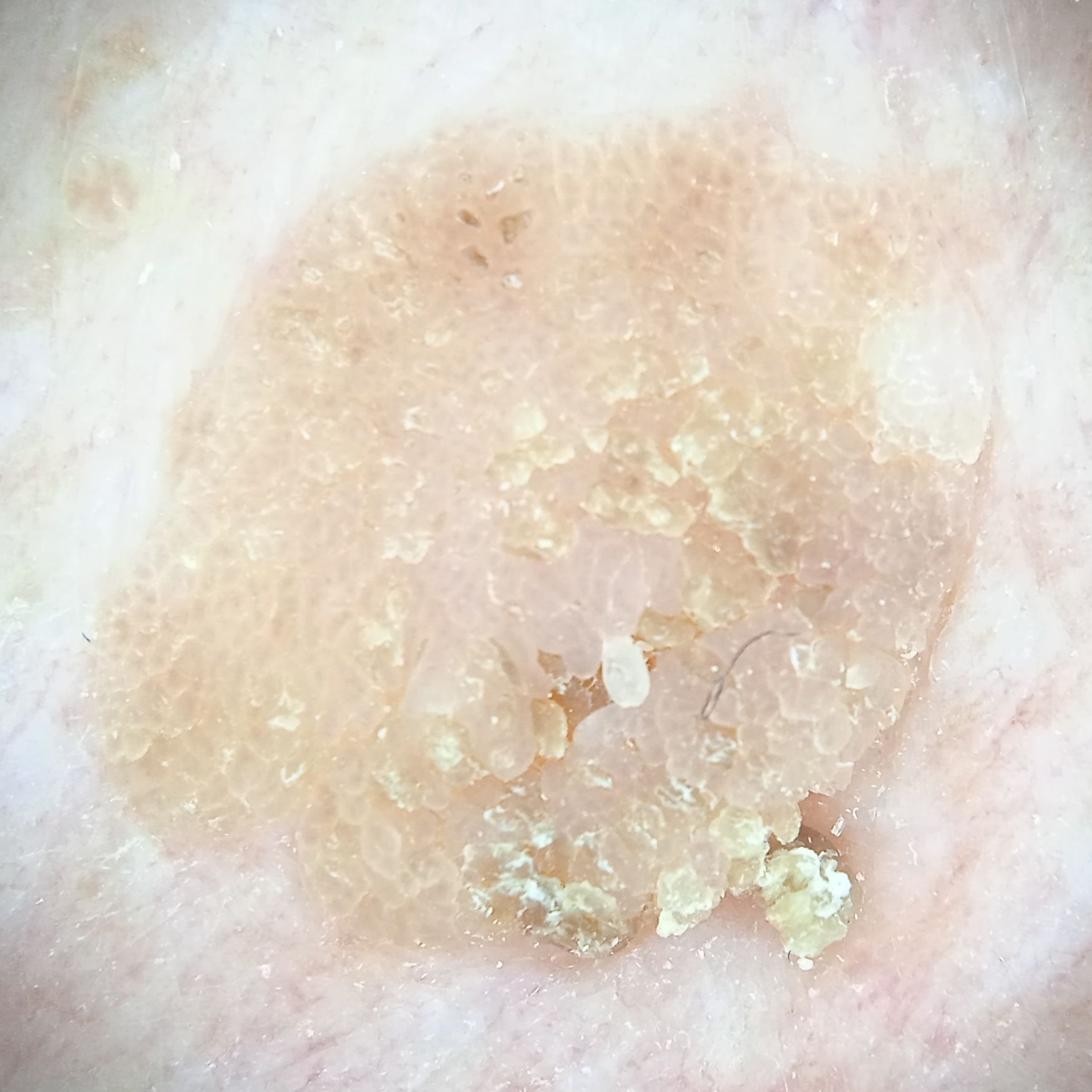The lesion was assessed as a seborrheic keratosis.